A moderate number of moles by the patient's own estimate · the patient says their skin tans without first burning · by self-report, a personal history of cancer · imaged for a research study, with no referral diagnosis recorded · a male subject age 65 — 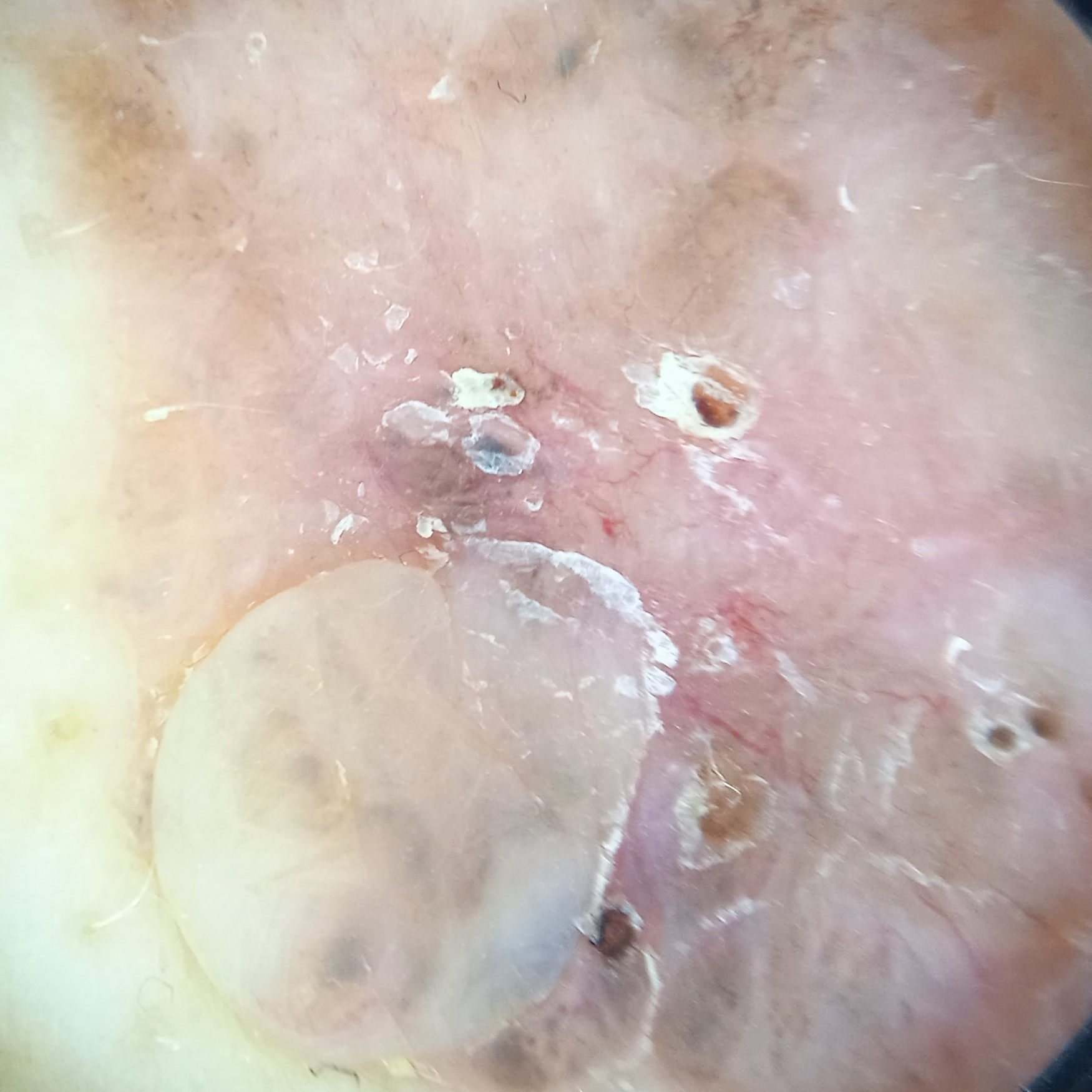Findings:
* diameter: 22.1 mm
* diagnosis: basal cell carcinoma (dermatologist consensus)